The affected area is the leg; lay graders estimated Monk Skin Tone 6 (US pool) or 4 (India pool); the contributor is 30–39, female; the contributor reports the lesion is raised or bumpy; symptoms reported: pain; reported duration is about one day; the patient considered this skin that appeared healthy to them; a close-up photograph:
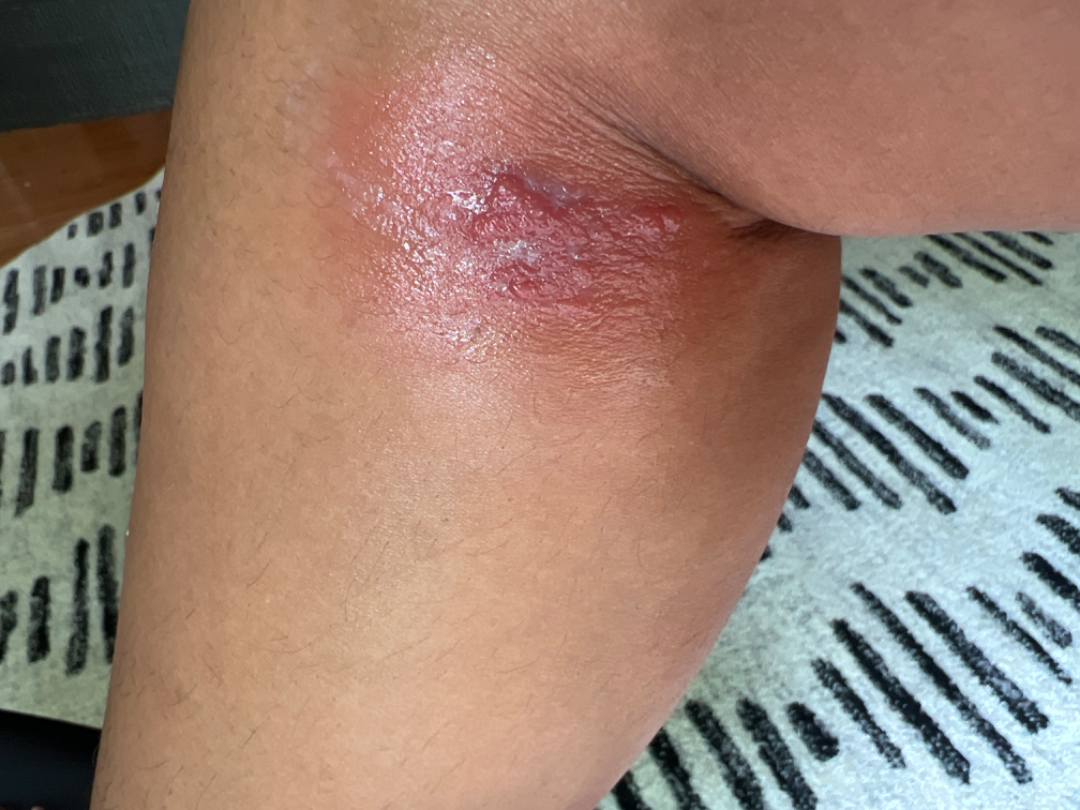differential: the leading impression is Cellulitis.